The patient is a female aged around 25 · a dermatoscopic image of a skin lesion: 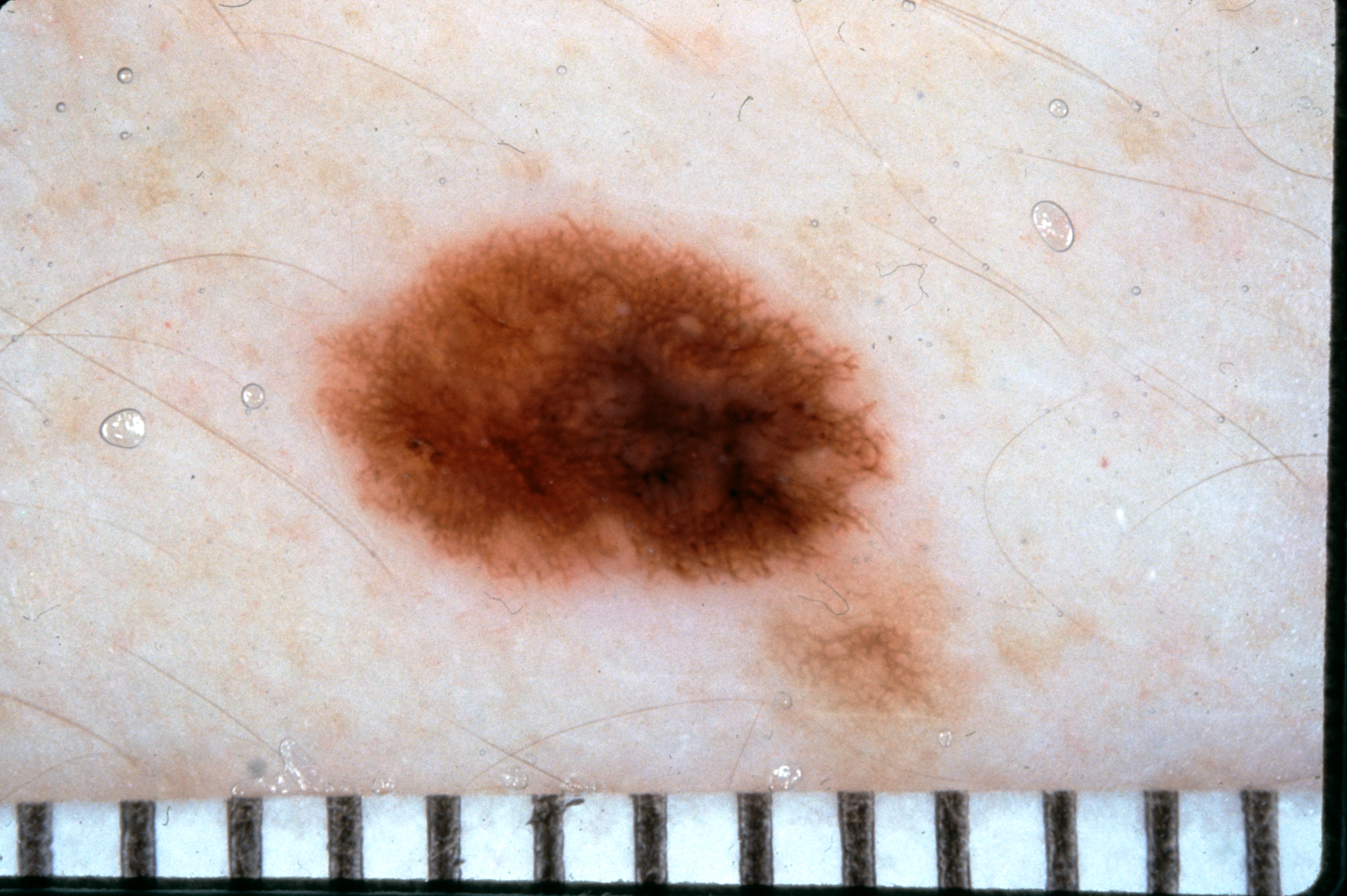With coordinates (x1, y1, x2, y2), the visible lesion spans bbox(326, 224, 894, 588). The lesion takes up a moderate portion of the field. Dermoscopic examination shows pigment network. On biopsy, the diagnosis was a melanoma, a malignancy.